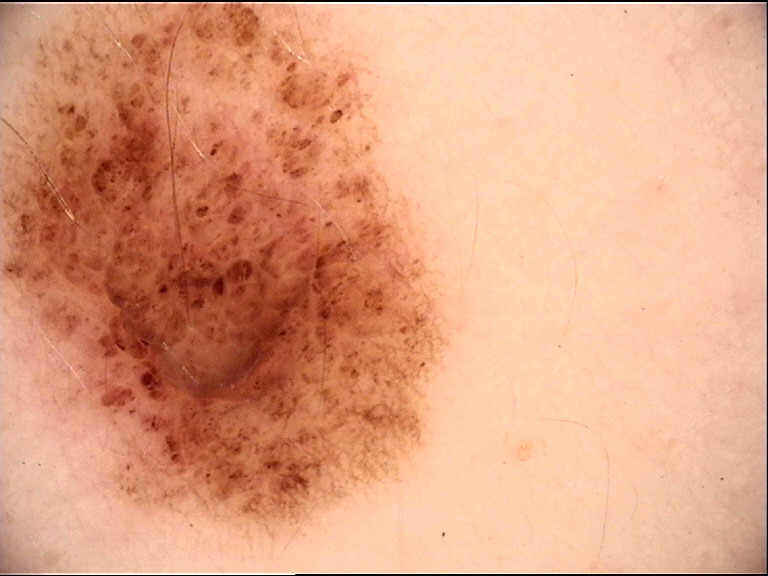Diagnosed as a compound nevus.